Close-up view; the lesion involves the arm.
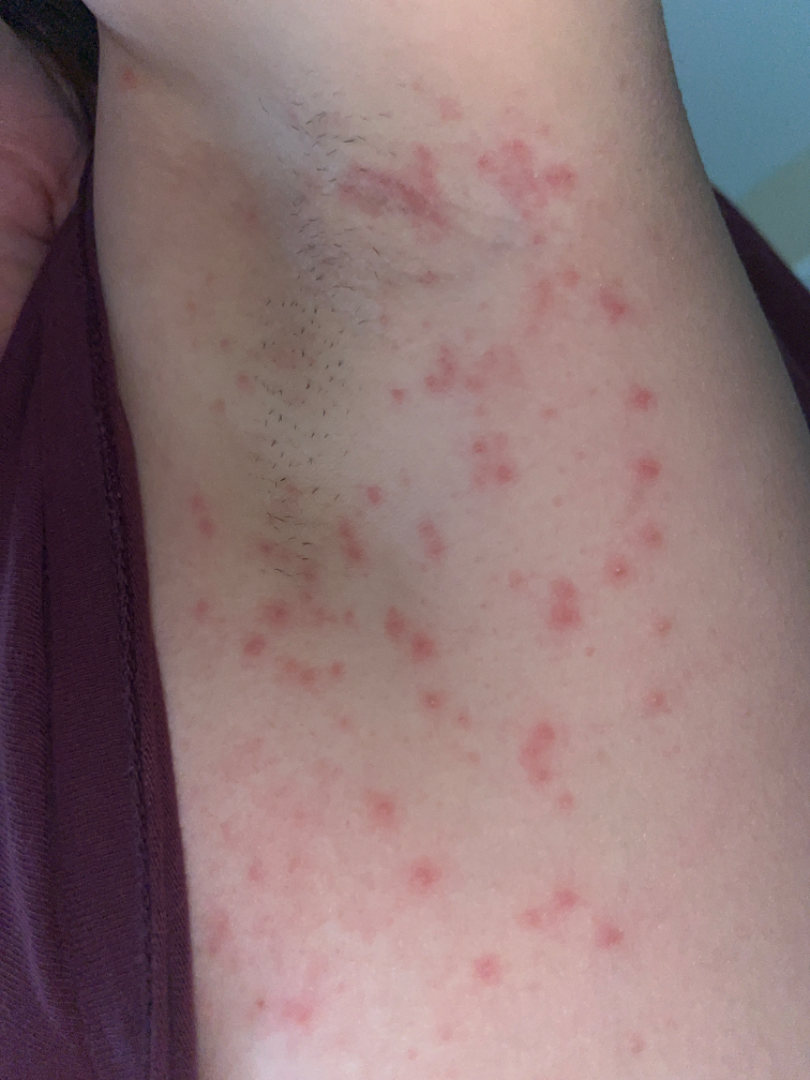Impression:
The skin condition could not be confidently assessed from this image.